A skin lesion imaged with a dermatoscope: 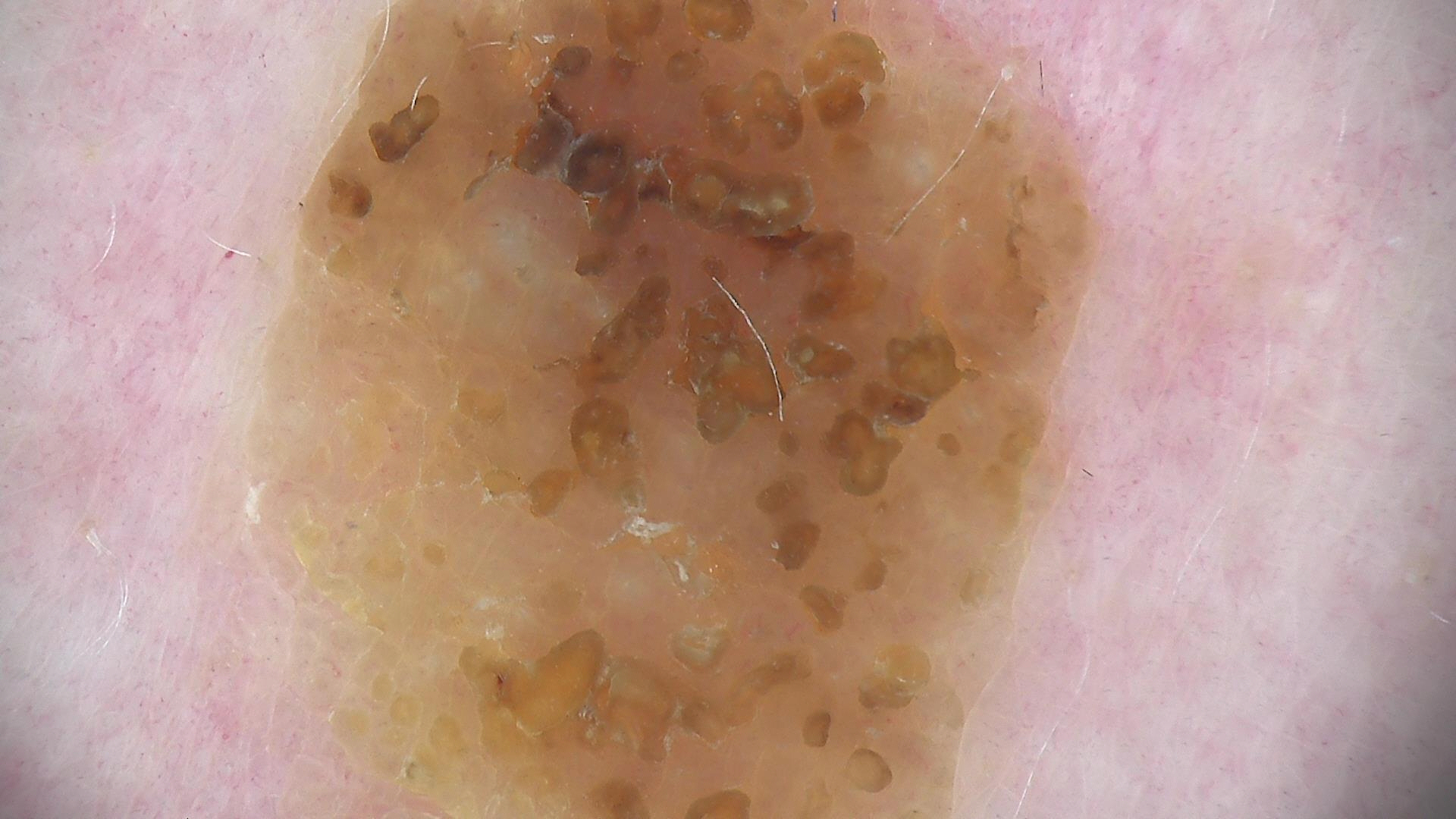The diagnosis was a keratinocytic, benign lesion — a seborrheic keratosis.